Skin tone: Fitzpatrick III. The patient reports associated joint pain and shortness of breath. The lesion involves the arm. Reported duration is one to four weeks. The photograph was taken at an angle. Reported lesion symptoms include bothersome appearance, itching and bleeding. The lesion is described as raised or bumpy, fluid-filled and rough or flaky.
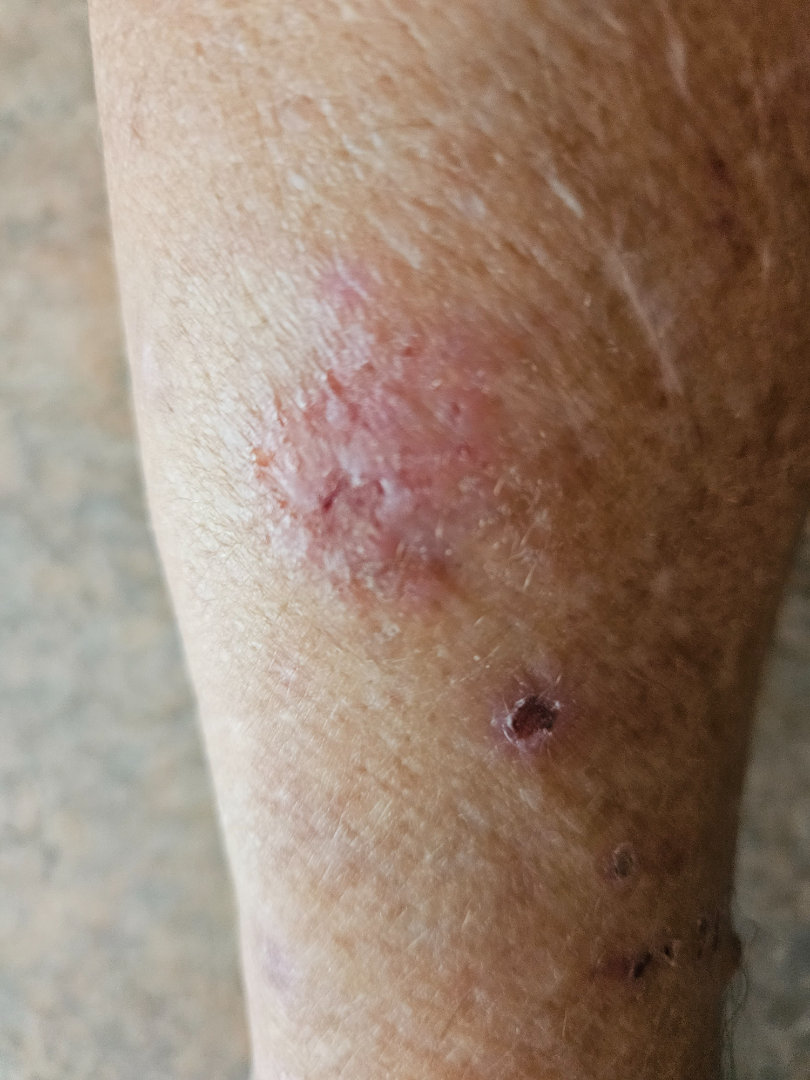Impression:
The reviewer was unable to grade this case for skin condition.